A dermoscopic image of a skin lesion.
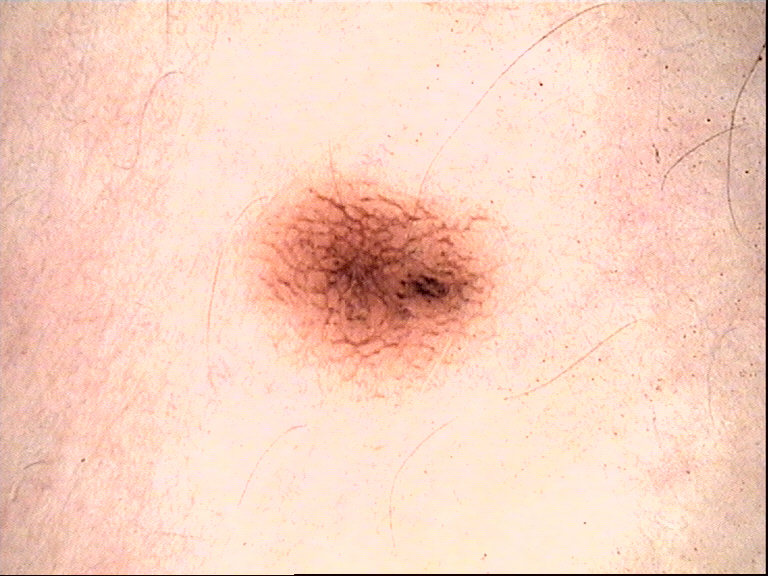Case:
• diagnosis: dysplastic junctional nevus (expert consensus)